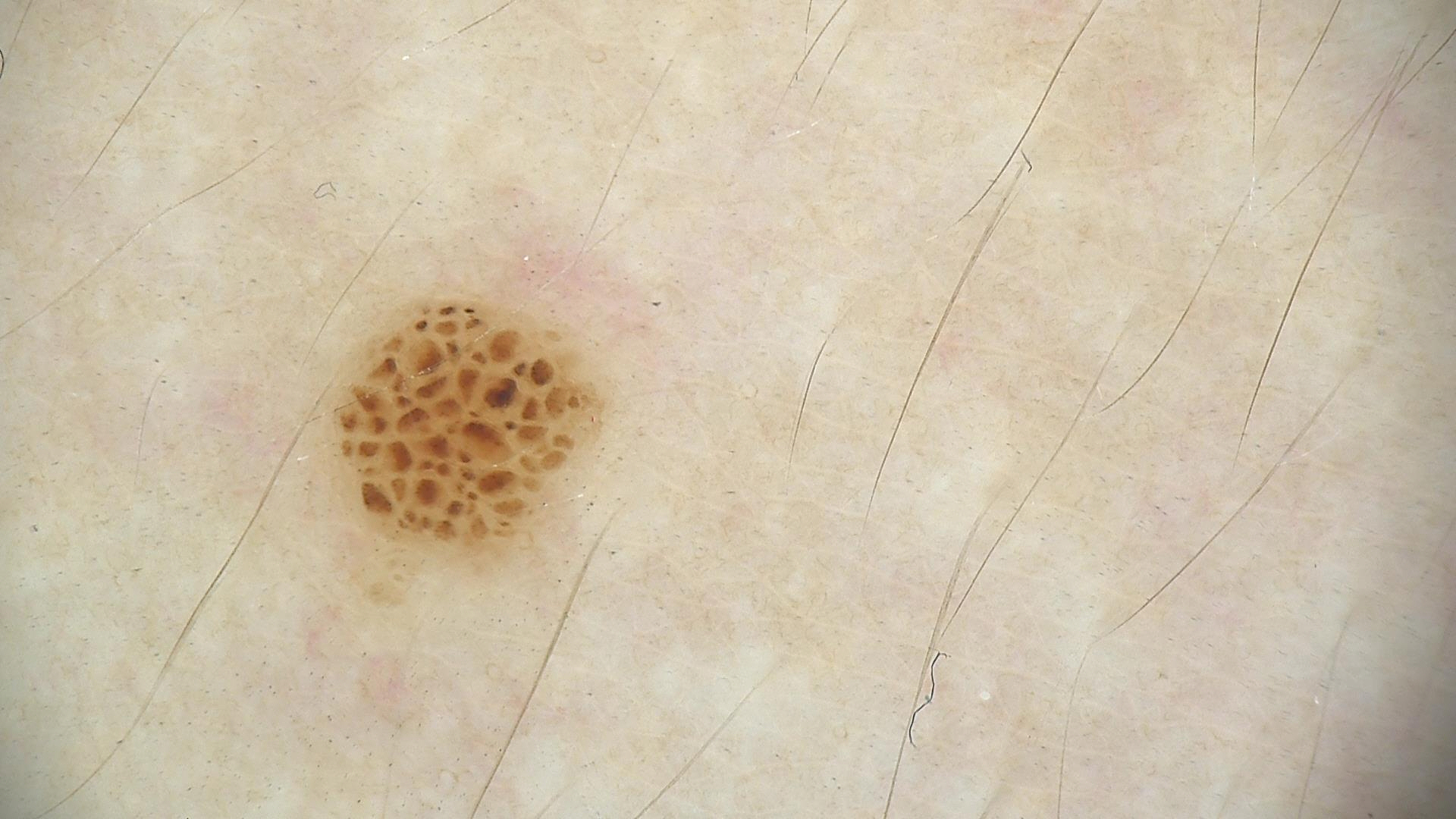Findings:
A dermoscopy image of a single skin lesion.
Conclusion:
Classified as a benign lesion — a dysplastic junctional nevus.